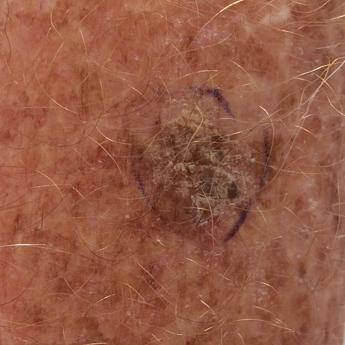A clinical photo of a skin lesion taken with a smartphone. The chart notes pesticide exposure, no prior skin cancer (patient or family), and no alcohol use. A male subject 87 years old. The lesion is on a forearm. The lesion measures 10 × 10 mm. The patient reports that the lesion itches, is elevated, and has bled. The clinical impression was an actinic keratosis.